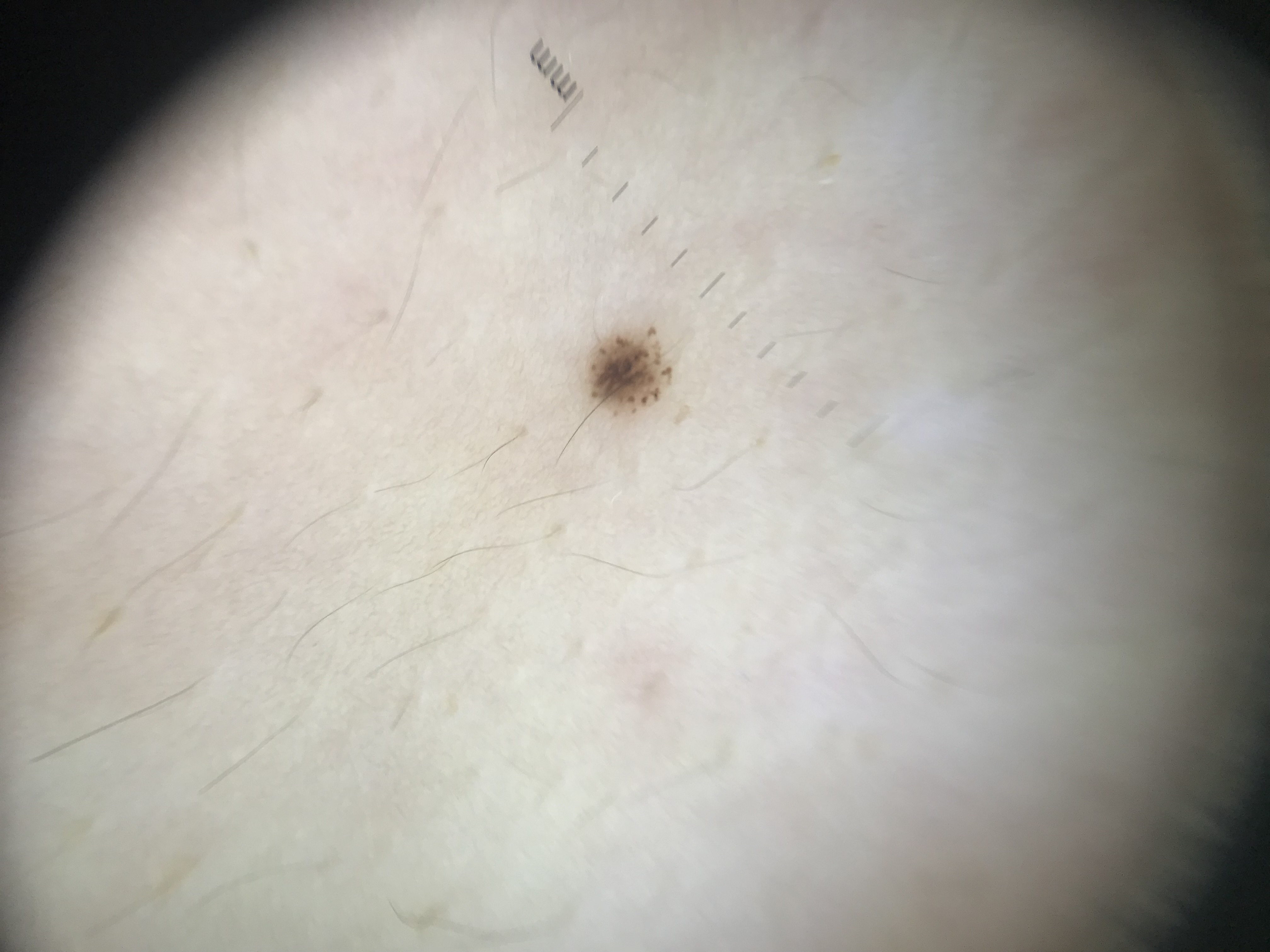image type: dermatoscopy, label: dysplastic junctional nevus (expert consensus).